The photograph was taken at an angle: 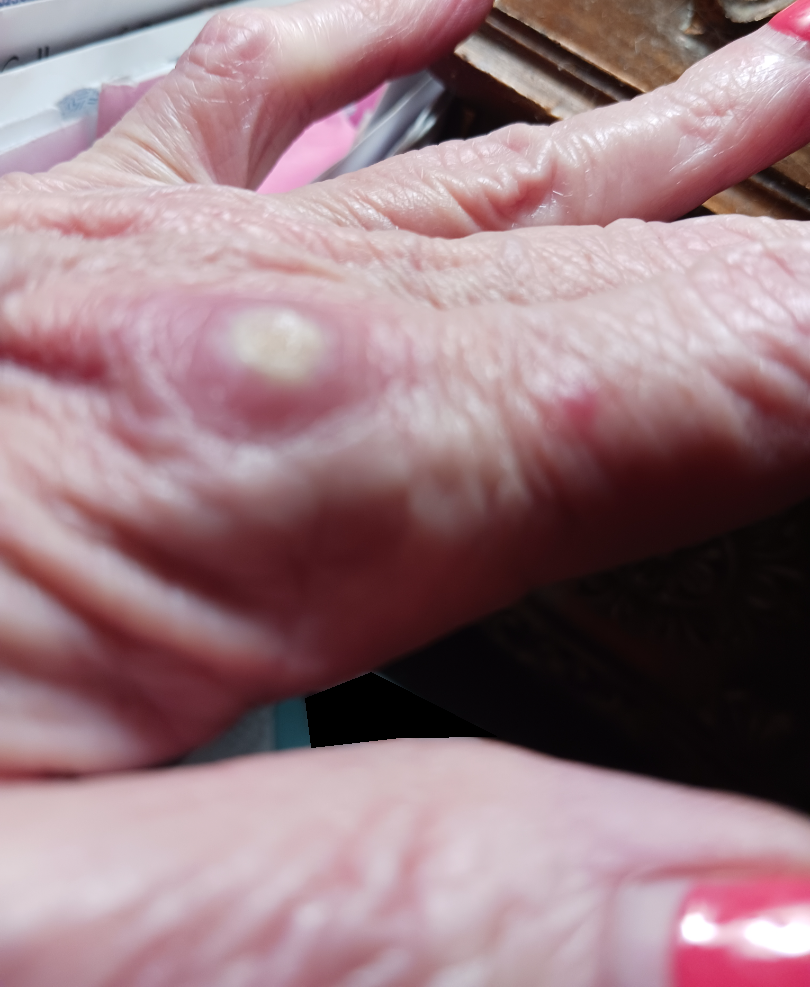skin tone: non-clinician graders estimated MST 2
present for: one to four weeks
surface texture: raised or bumpy
differential diagnosis: the leading consideration is SCC/SCCIS